The photograph is a close-up of the affected area · the lesion involves the arm, leg and top or side of the foot: 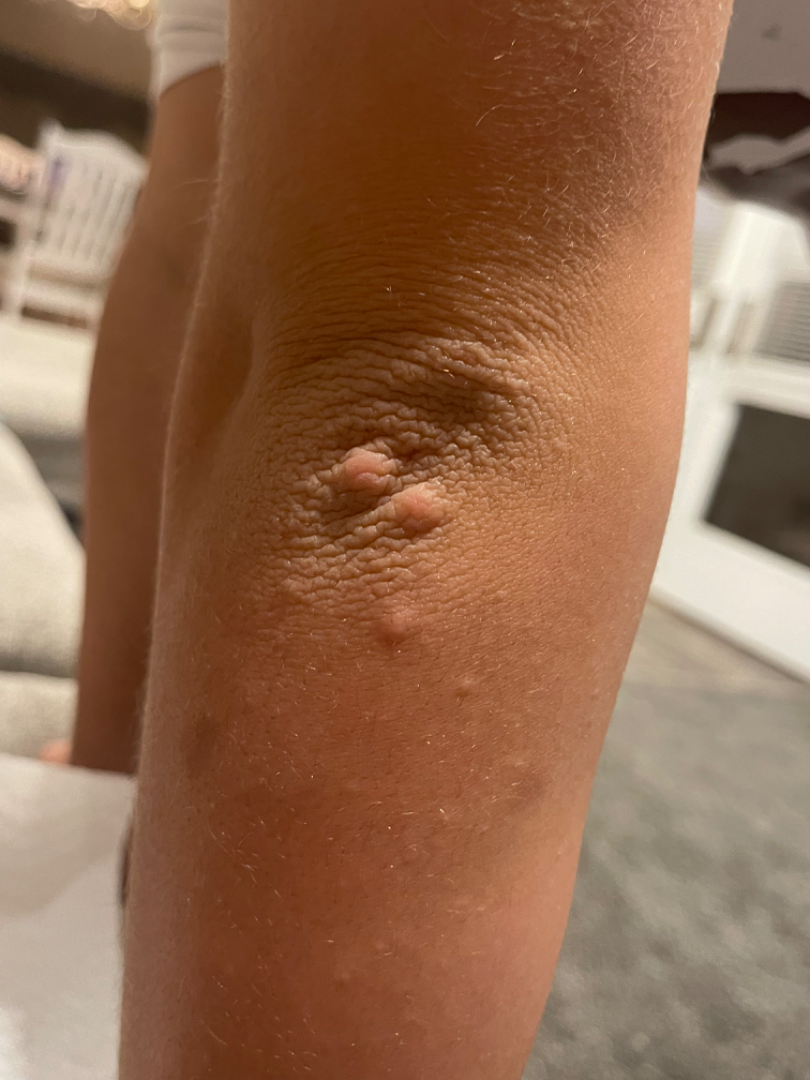Impression: The case was difficult to assess from the available photograph.